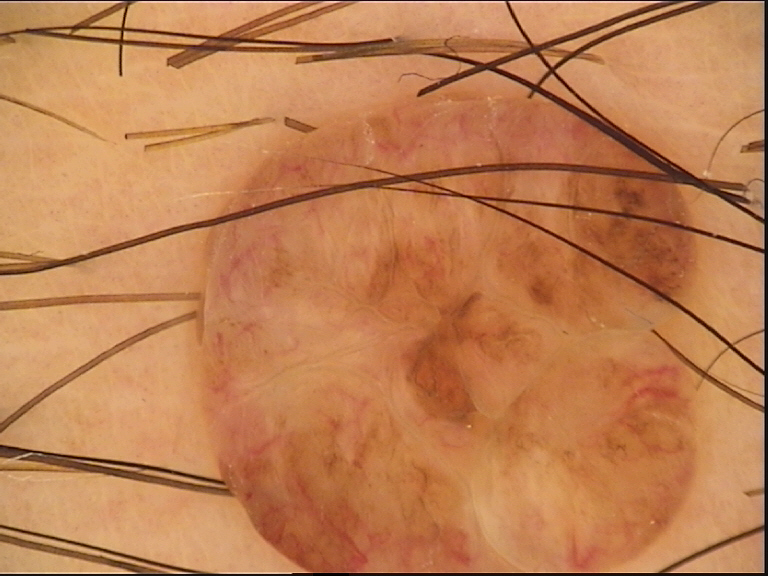Findings:
– image type · dermoscopy
– classification · banal
– class · dermal nevus (expert consensus)